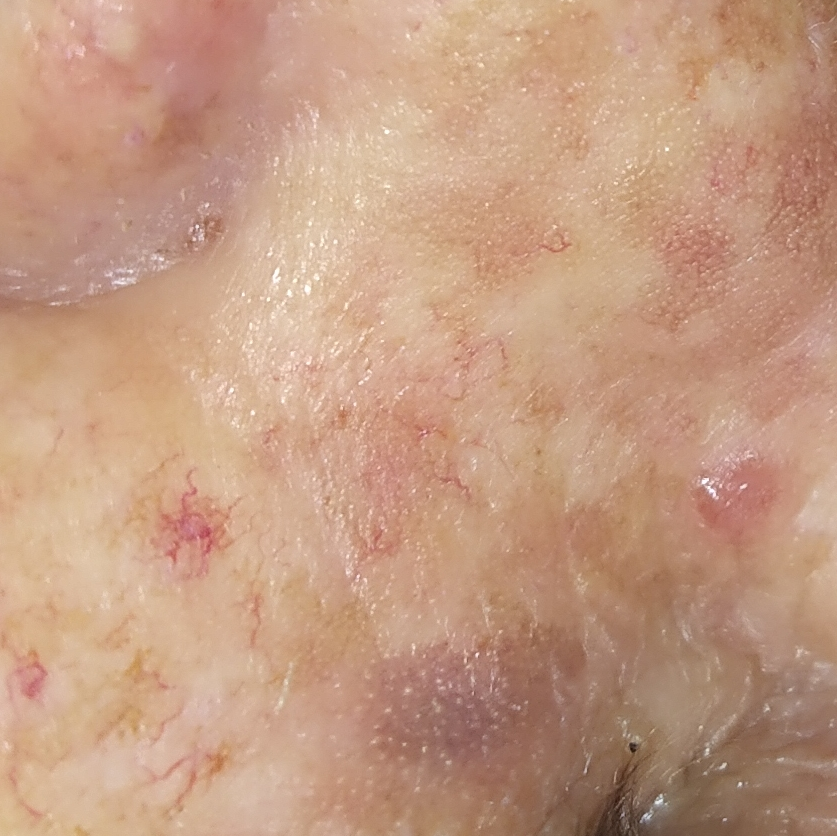A clinical close-up photograph of a skin lesion.
A female subject aged 67.
Located on the nose.
By the patient's account, the lesion has not bled.
Histopathology confirmed a basal cell carcinoma.